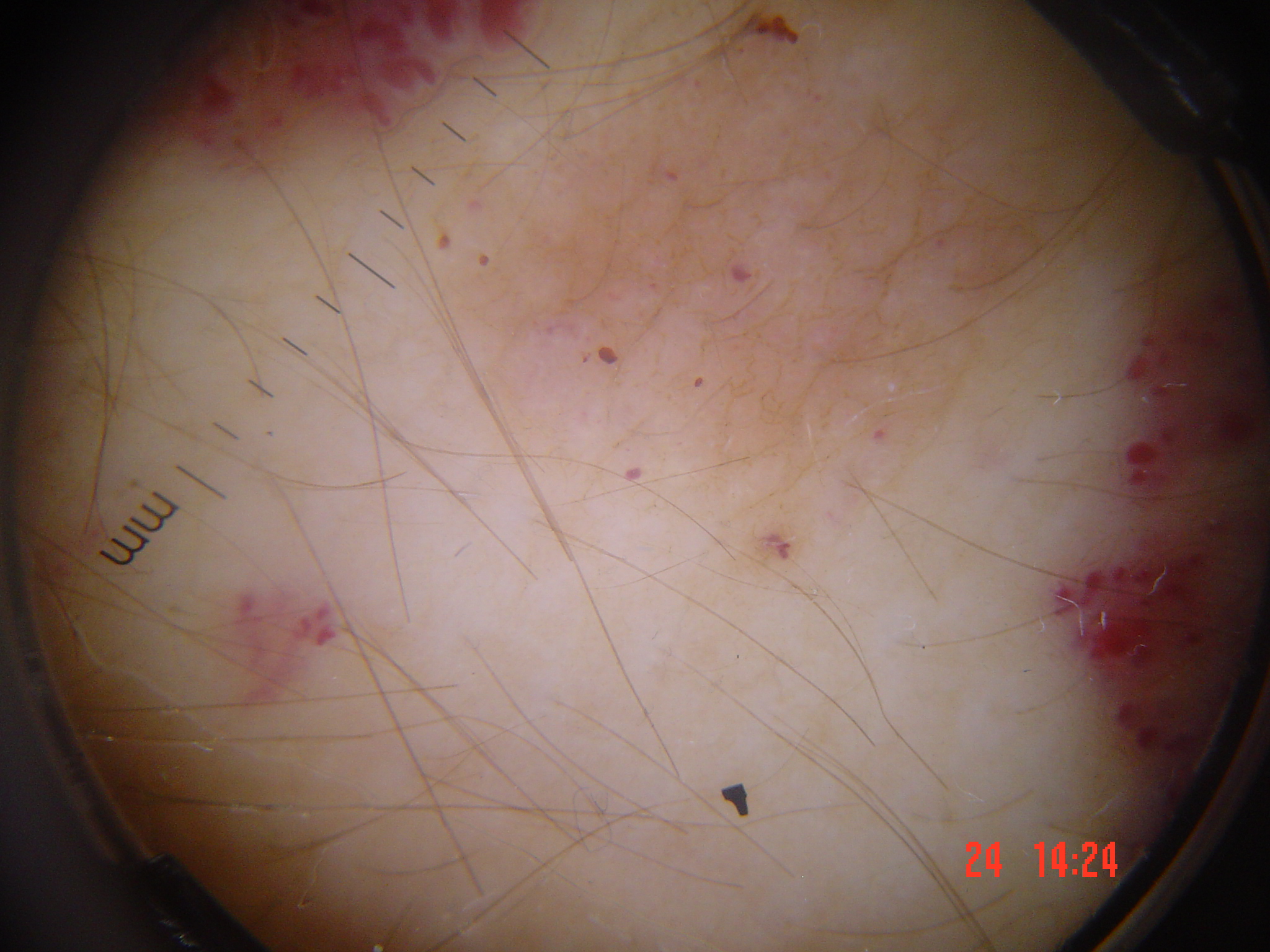Conclusion: Classified as a lymphangioma.